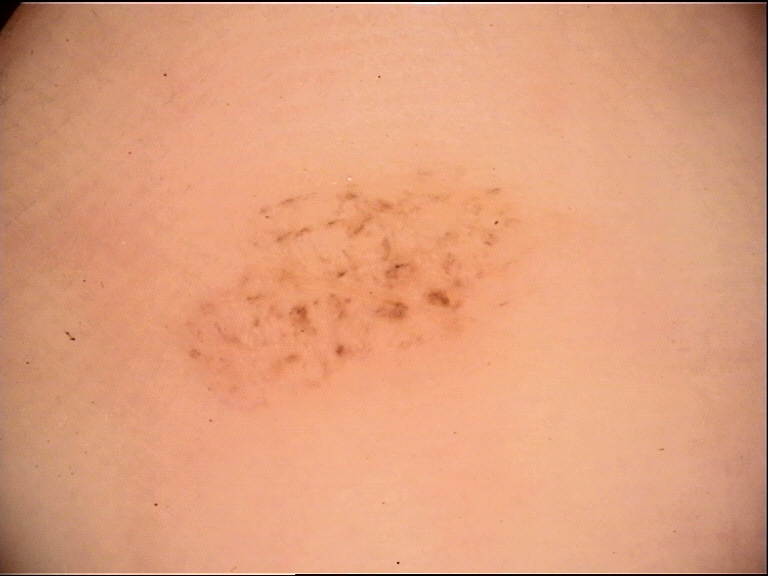Summary:
A dermoscopy image of a single skin lesion.
Impression:
Consistent with an acral dysplastic junctional nevus.